A dermatoscopic image of a skin lesion: 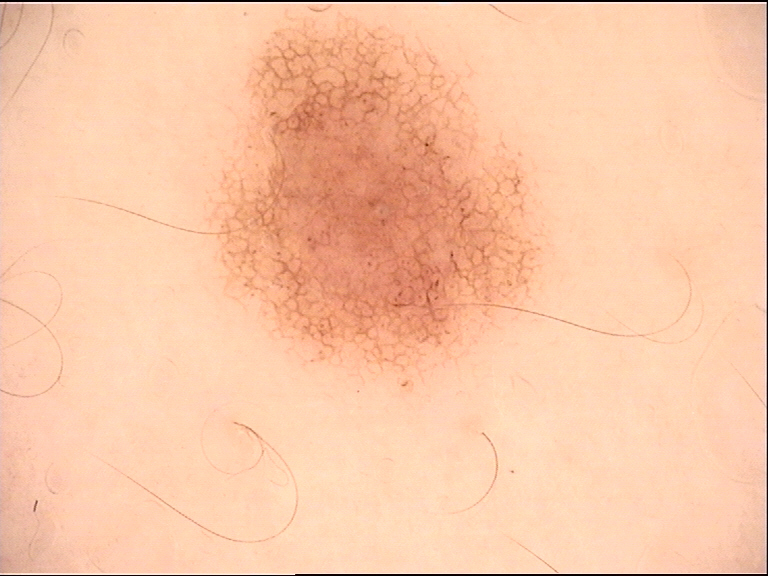Consistent with a dysplastic junctional nevus.